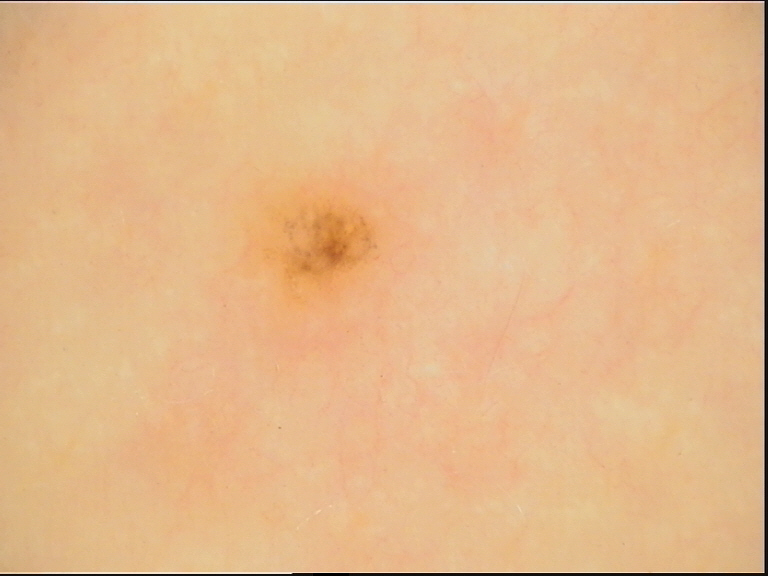{"image": "dermatoscopy", "diagnosis": {"name": "dysplastic junctional nevus", "code": "jd", "malignancy": "benign", "super_class": "melanocytic", "confirmation": "expert consensus"}}